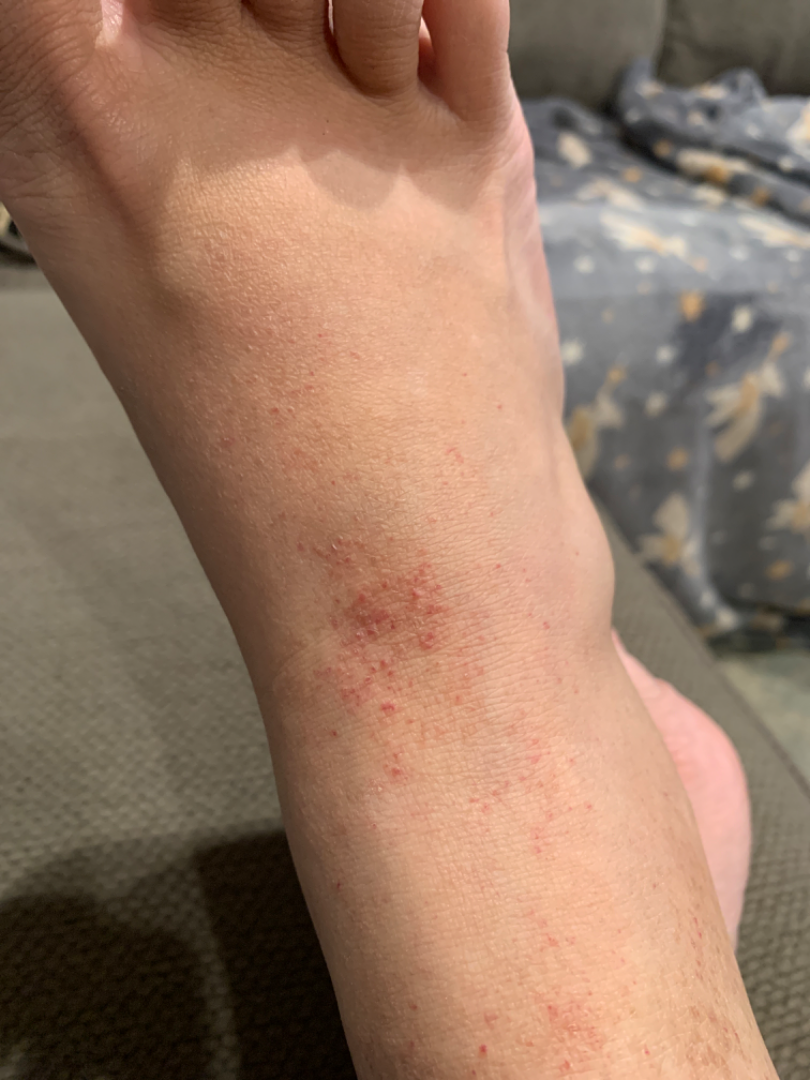Review:
On photographic review, Pigmented purpuric eruption (weight 0.35); Lichen Simplex Chronicus (weight 0.21); Eczema (weight 0.20); Leukocytoclastic Vasculitis (weight 0.13); Allergic Contact Dermatitis (weight 0.11).